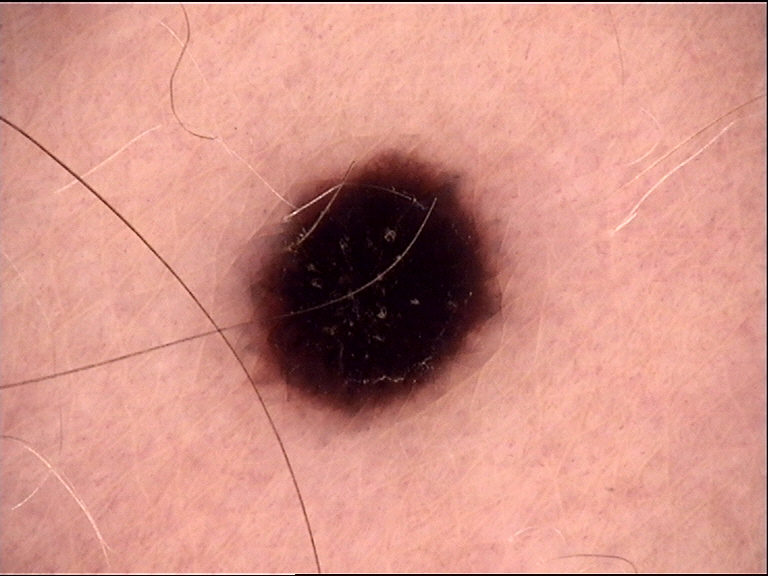image = dermoscopy, diagnostic label = dysplastic junctional nevus (expert consensus).